A dermoscopy image of a single skin lesion: 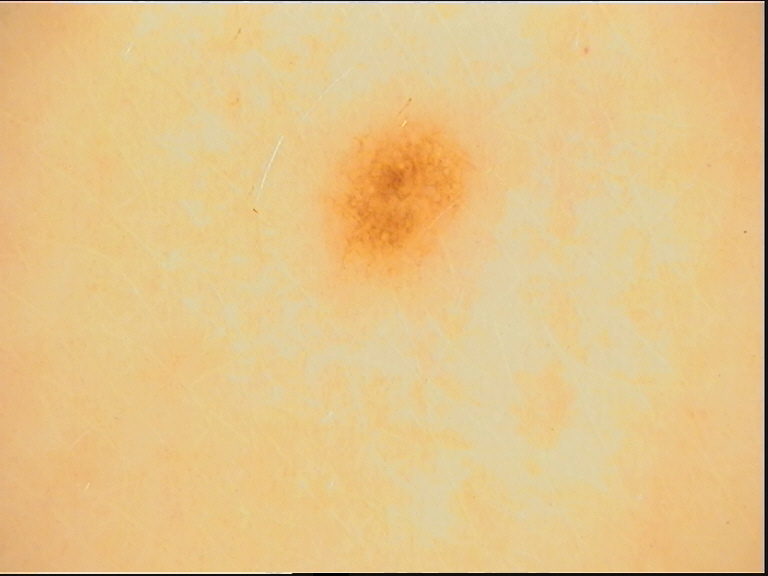Case:
– class: dysplastic junctional nevus (expert consensus)